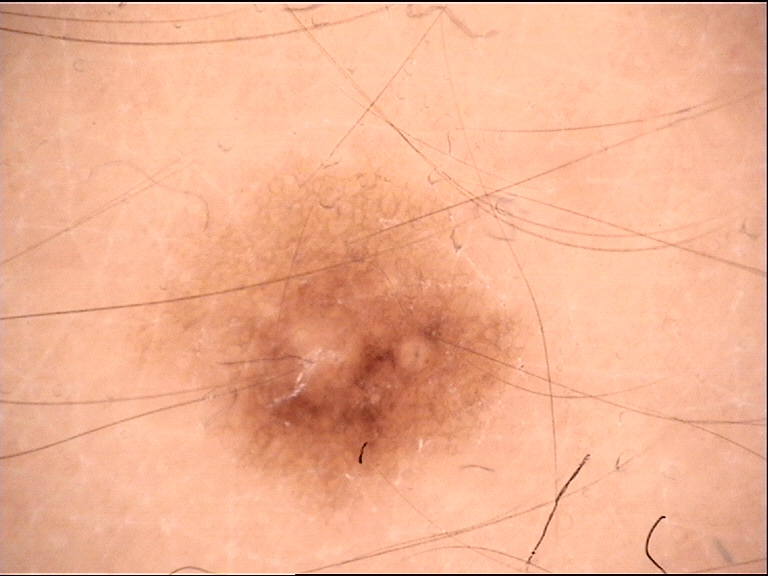Case:
The morphology is that of a banal lesion.
Conclusion:
Consistent with a junctional nevus.